A clinical close-up photograph of a skin lesion. A male patient in their late 50s. The patient was assessed as skin type II:
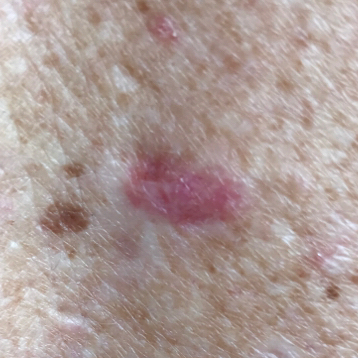Q: What is the anatomic site?
A: the back
Q: What are the lesion's dimensions?
A: 7 × 5 mm
Q: What does the patient describe?
A: elevation
Q: What is this lesion?
A: basal cell carcinoma (biopsy-proven)